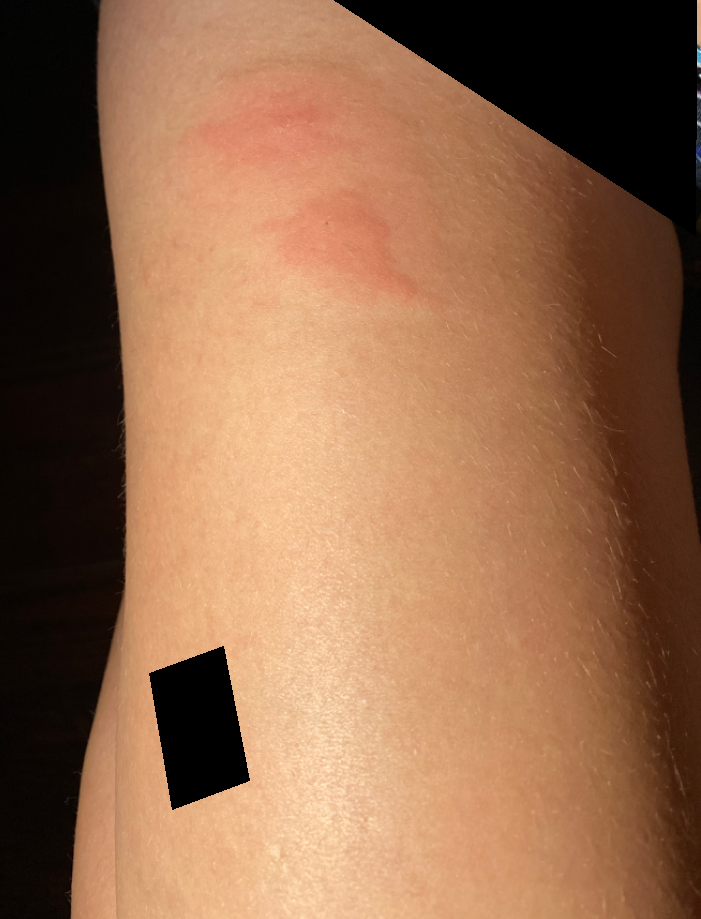<summary>
<assessment>unable to determine</assessment>
</summary>